A dermoscopic image of a skin lesion.
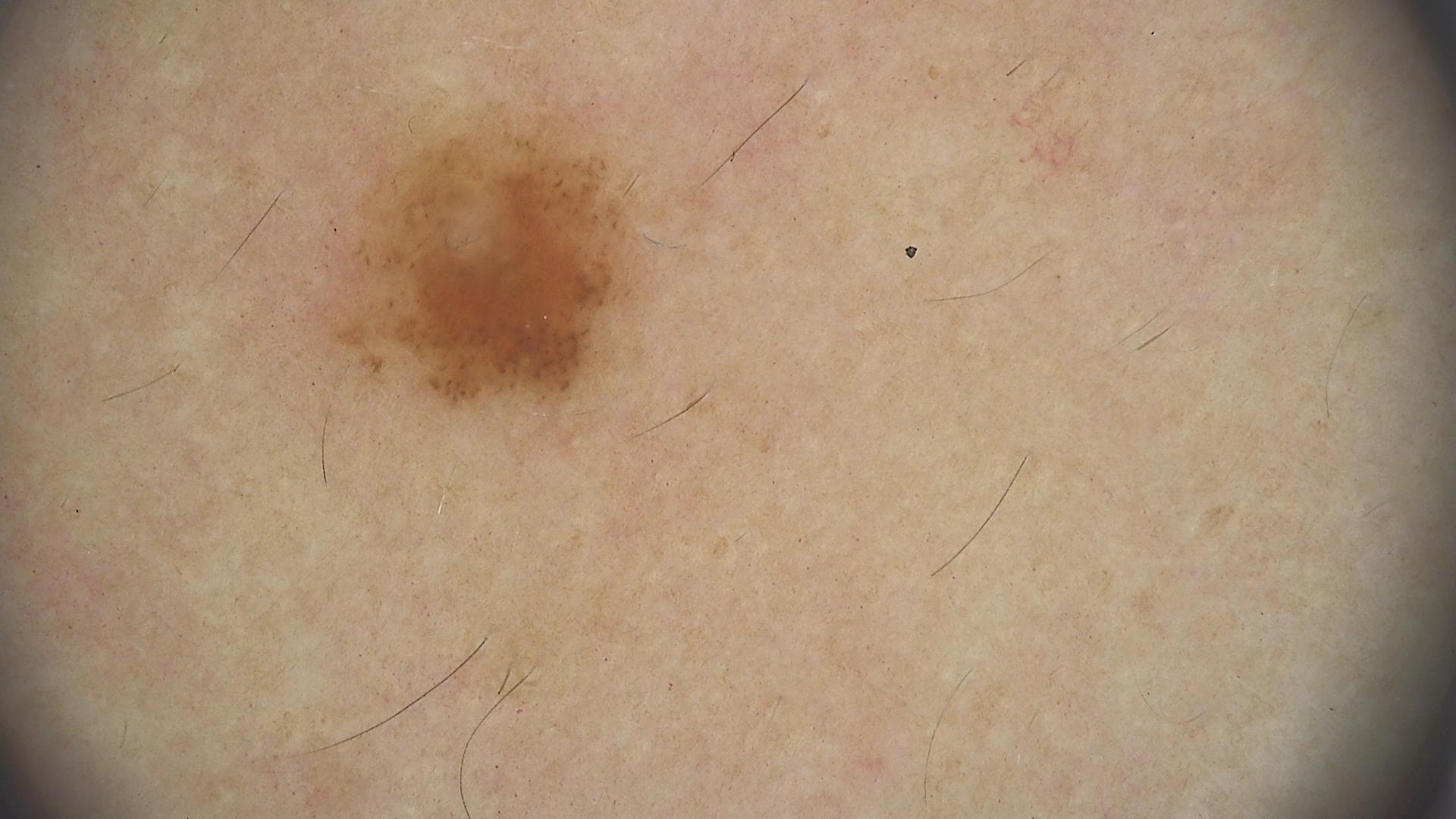Conclusion:
The diagnosis was a benign lesion — a dysplastic junctional nevus.